This is a close-up image. The contributor is 30–39, female — 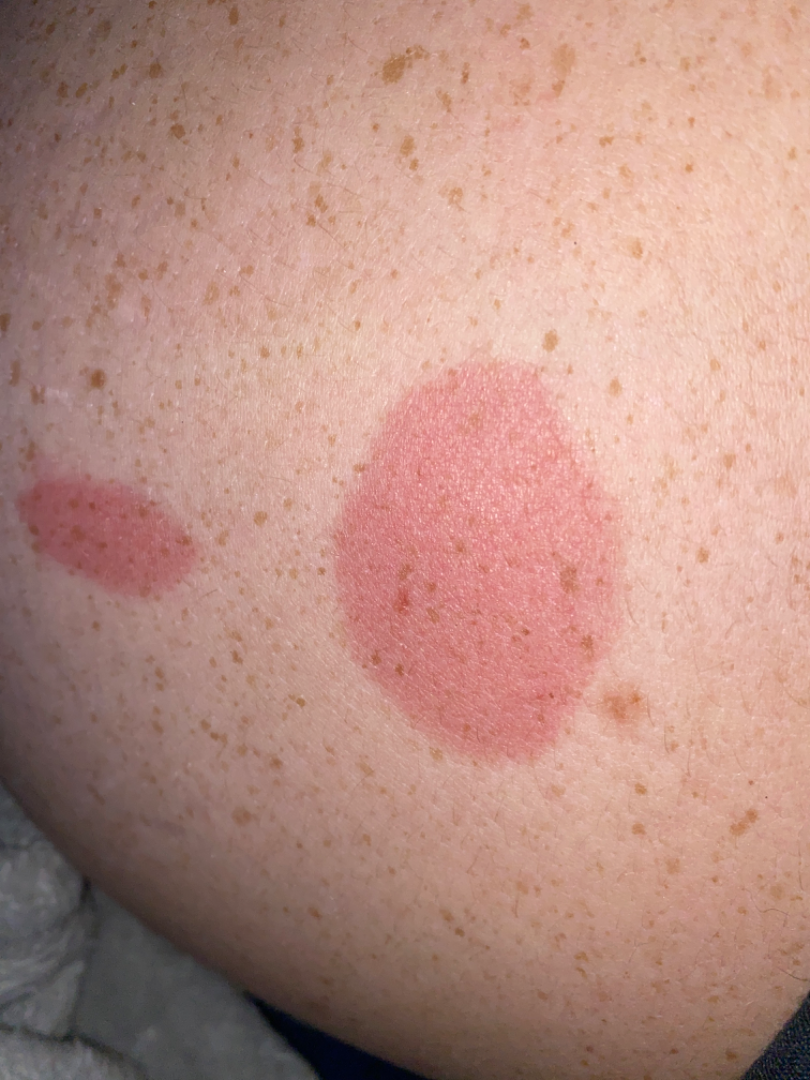assessment: not assessable
symptoms: none reported
systemic_symptoms: none reported
duration: about one day
texture: flat